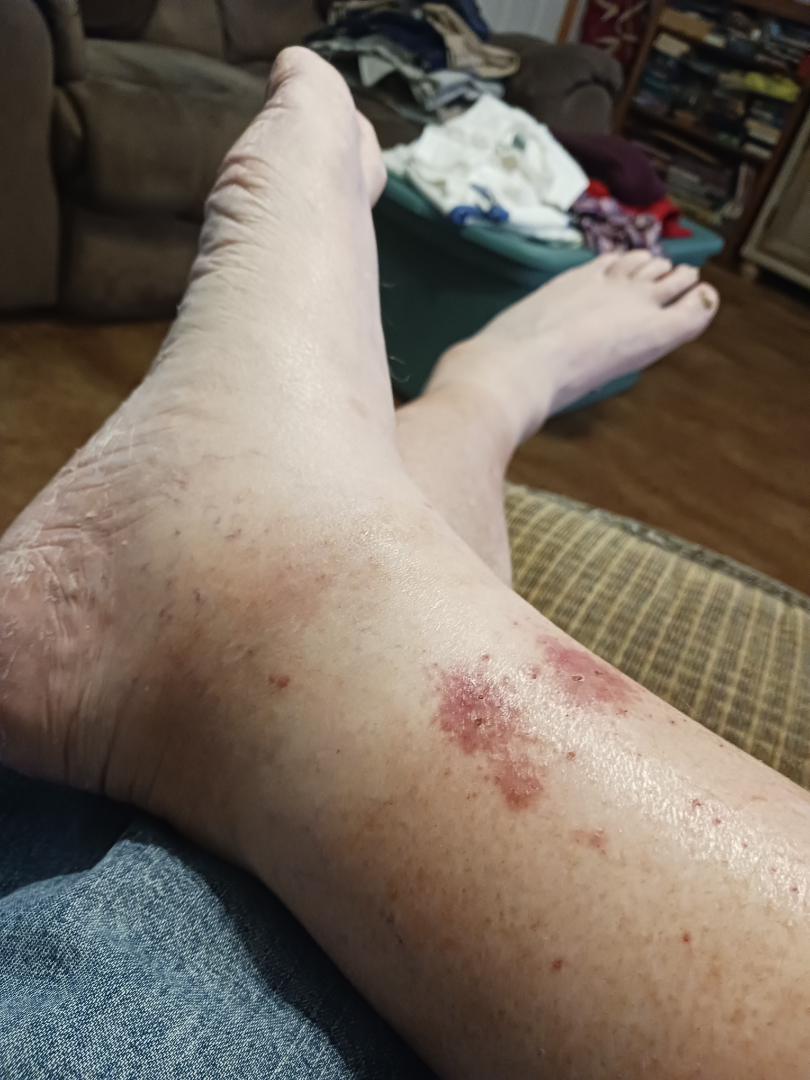affected area = leg; lesion texture = rough or flaky; reported symptoms = bothersome appearance, darkening and itching; contributor = male, age 70–79; present for = one to four weeks; framing = at an angle; assessment = Pigmented purpuric eruption (favored).